A dermoscopic image of a skin lesion: 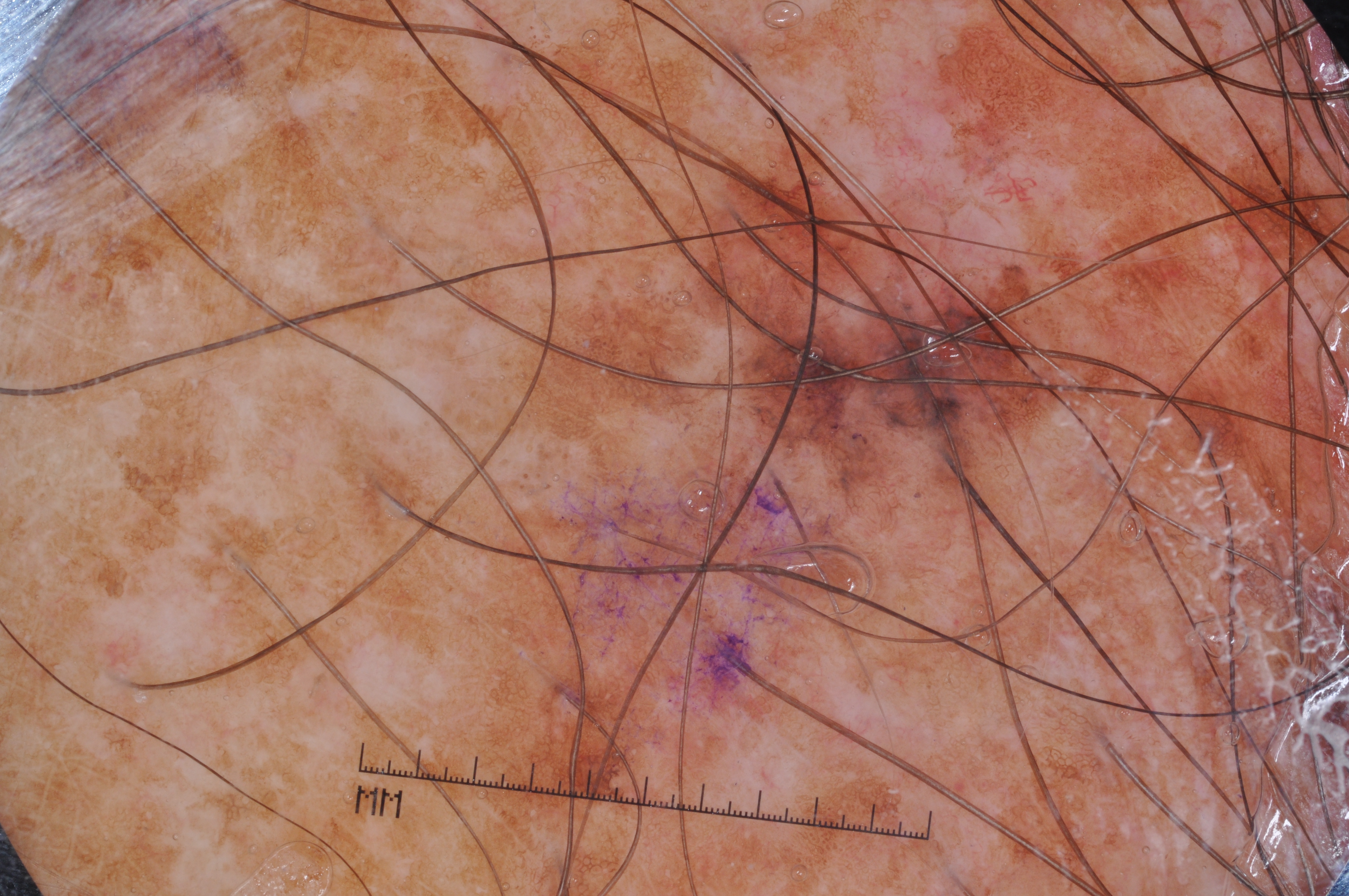dermoscopic features — milia-like cysts and pigment network; absent: negative network and streaks | lesion location — bbox=[513, 152, 1097, 541] | impression — a melanoma, a malignant lesion.